A skin lesion imaged with a dermatoscope:
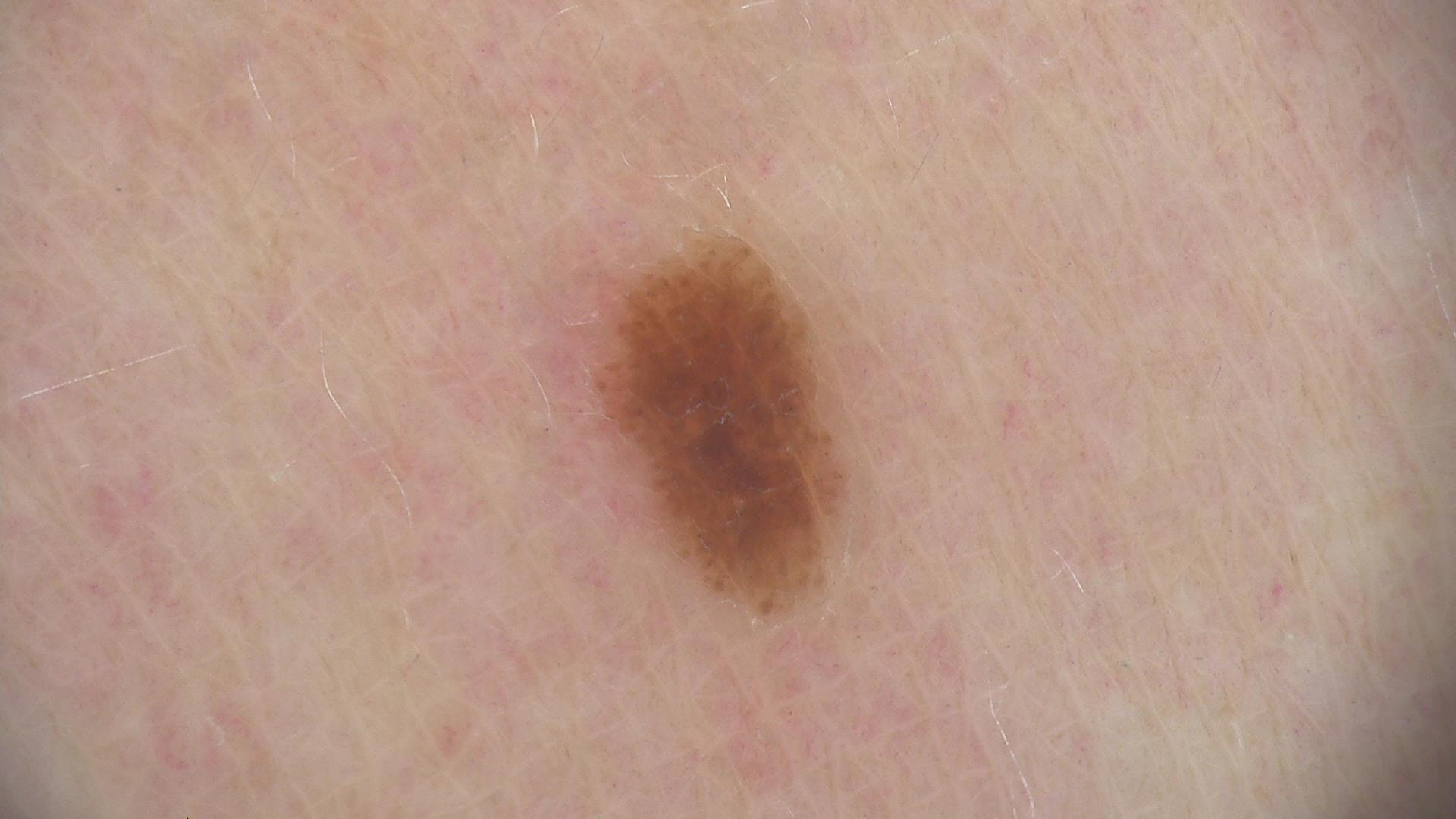Classified as a dysplastic junctional nevus.